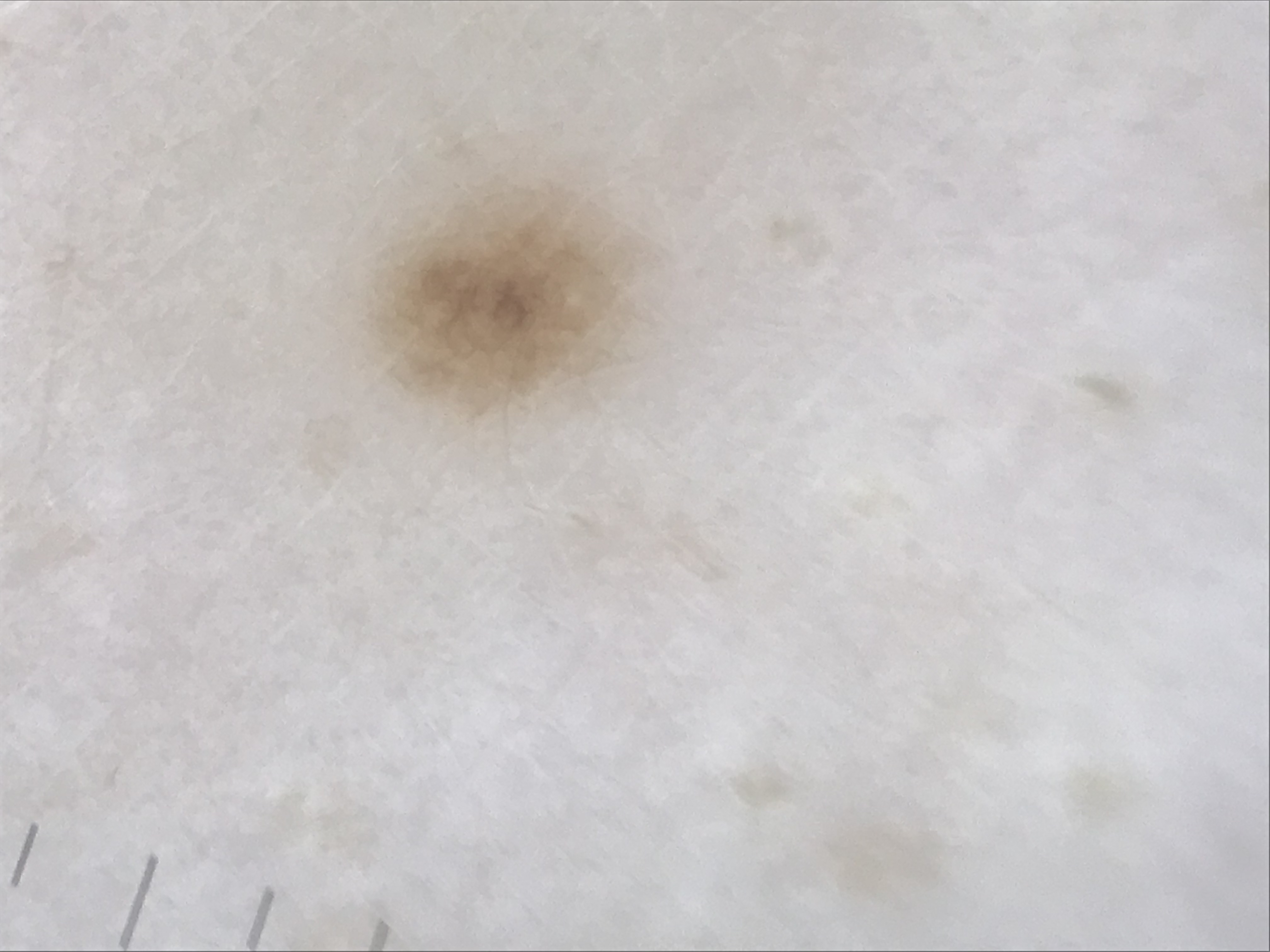Case: A dermoscopy image of a single skin lesion. This is a banal lesion. Impression: The diagnostic label was a junctional nevus.